The affected area is the arm. Skin tone: Fitzpatrick phototype II; lay reviewers estimated MST 3. The contributor reports the lesion is rough or flaky. The lesion is associated with itching. This is a close-up image. Female patient, age 50–59.
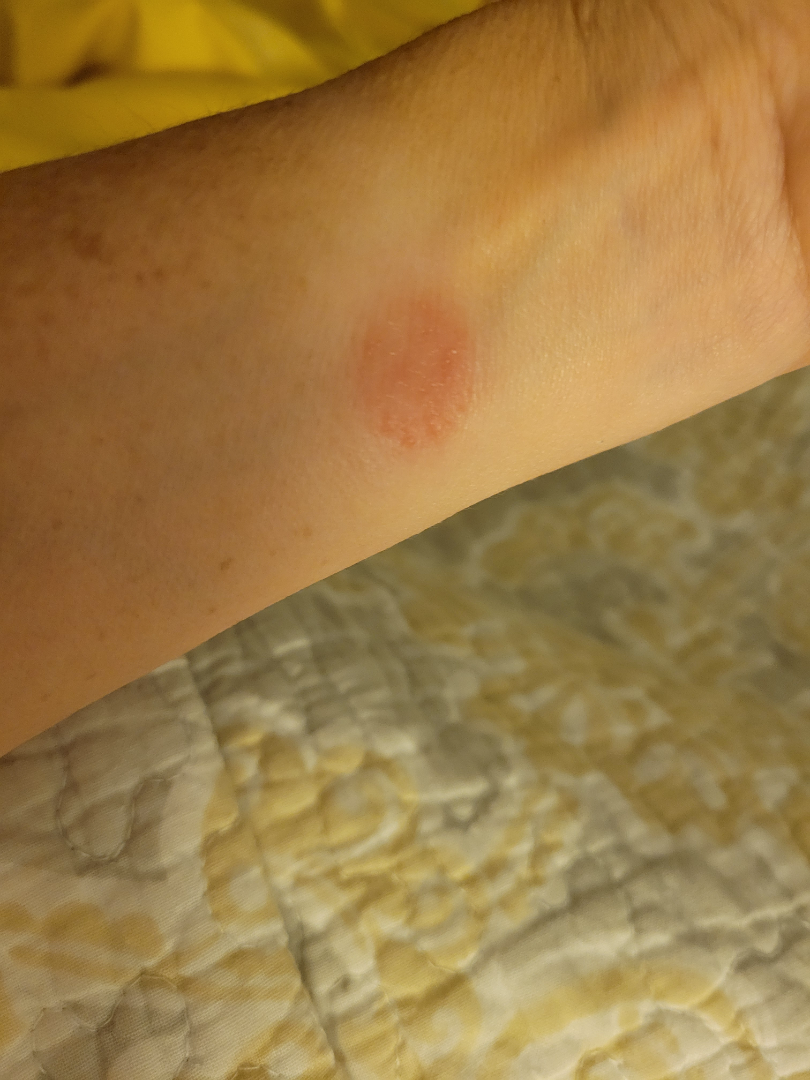differential: Eczema